The patient is 60–69, female; the patient described the issue as a rash; FST II; the patient also reports joint pain, fatigue and shortness of breath; reported lesion symptoms include bothersome appearance, enlargement, burning and pain; the photo was captured at a distance; located on the leg.
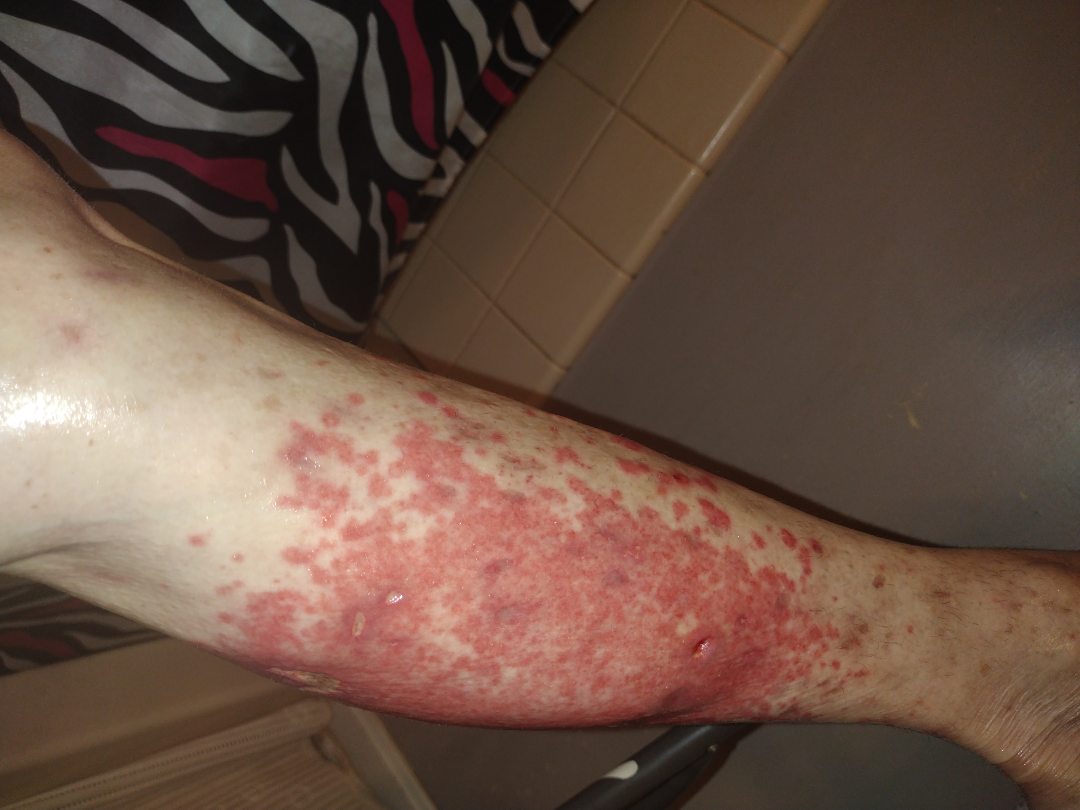The impression was split between Leukocytoclastic Vasculitis and Cellulitis; also on the differential is Impetigo.